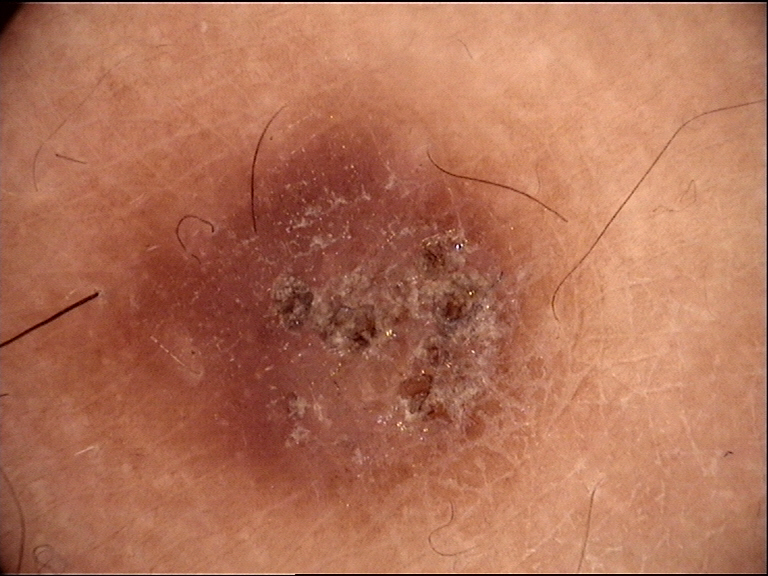Labeled as a fibro-histiocytic lesion — a dermatofibroma.